A macroscopic clinical photograph of a skin lesion · a female patient age 15 · acquired for a research image collection, with no referral diagnosis:
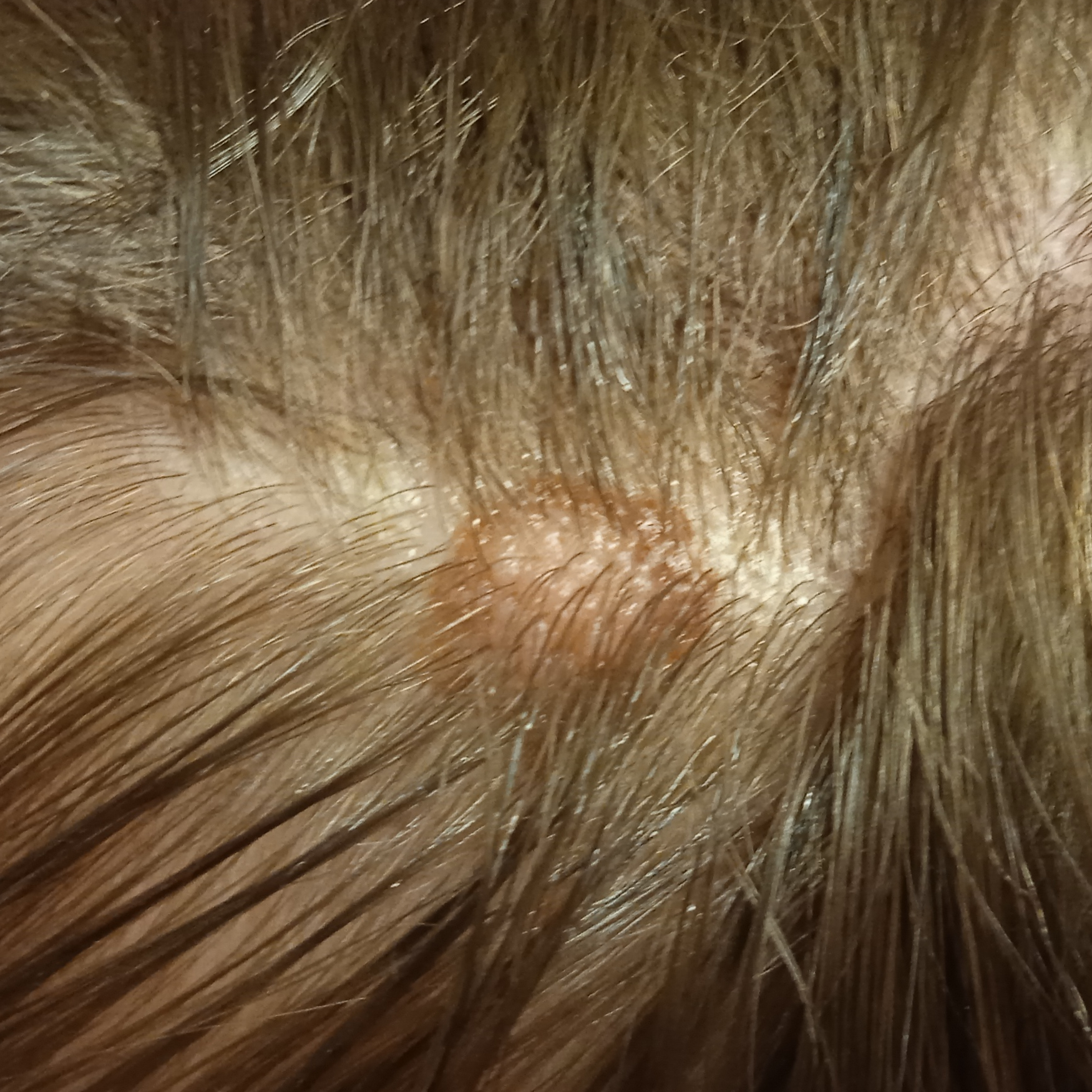site: the head; size: 9.1 mm; diagnostic label: melanocytic nevus (dermatologist consensus).